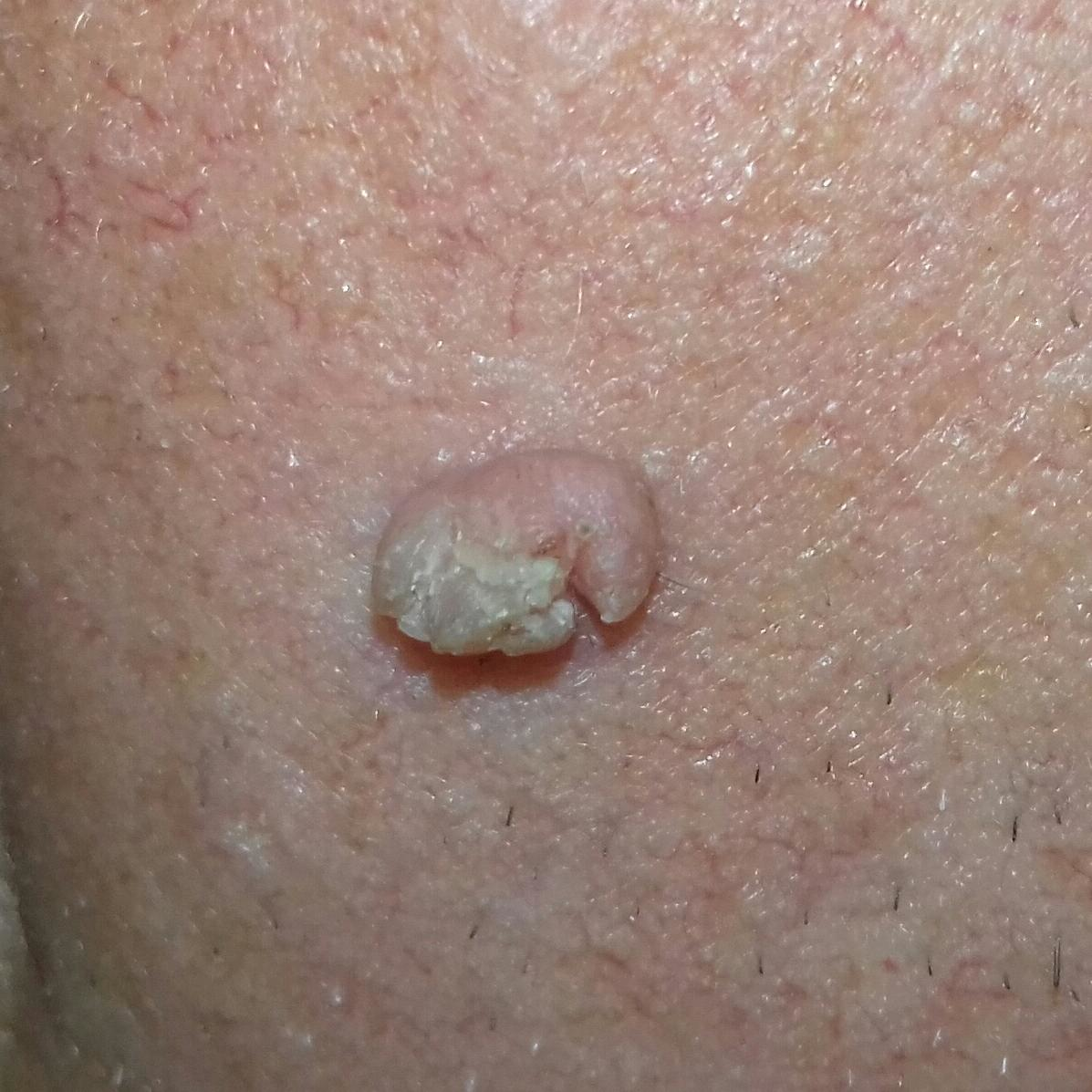Findings:
A male patient aged 68. The lesion was found on the face. Per patient report, the lesion has grown, itches, and is elevated, but has not changed.
Conclusion:
On biopsy, the diagnosis was an actinic keratosis.